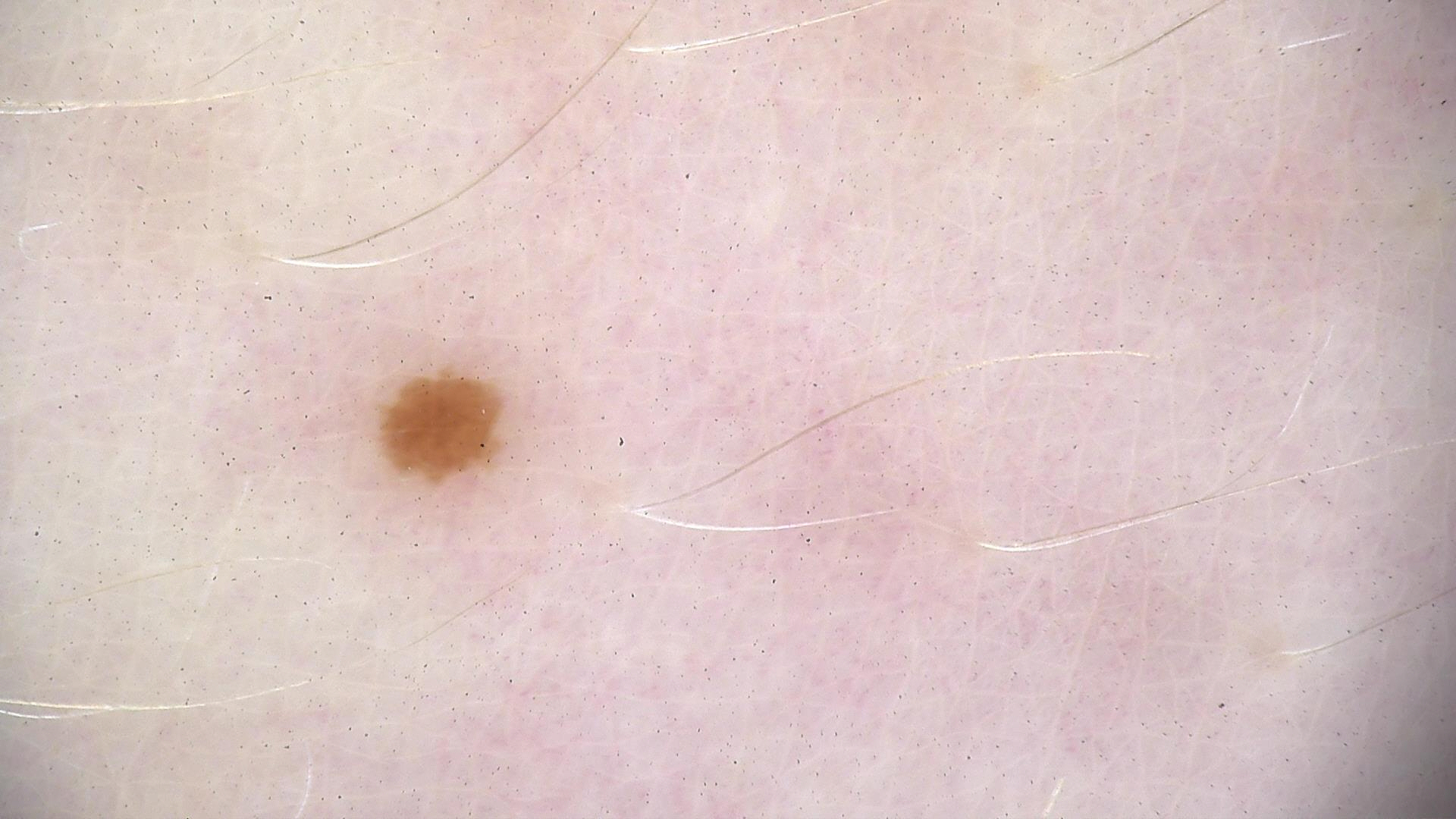A dermoscopic photograph of a skin lesion. The diagnosis was a benign lesion — a dysplastic junctional nevus.